A skin lesion imaged with a dermatoscope.
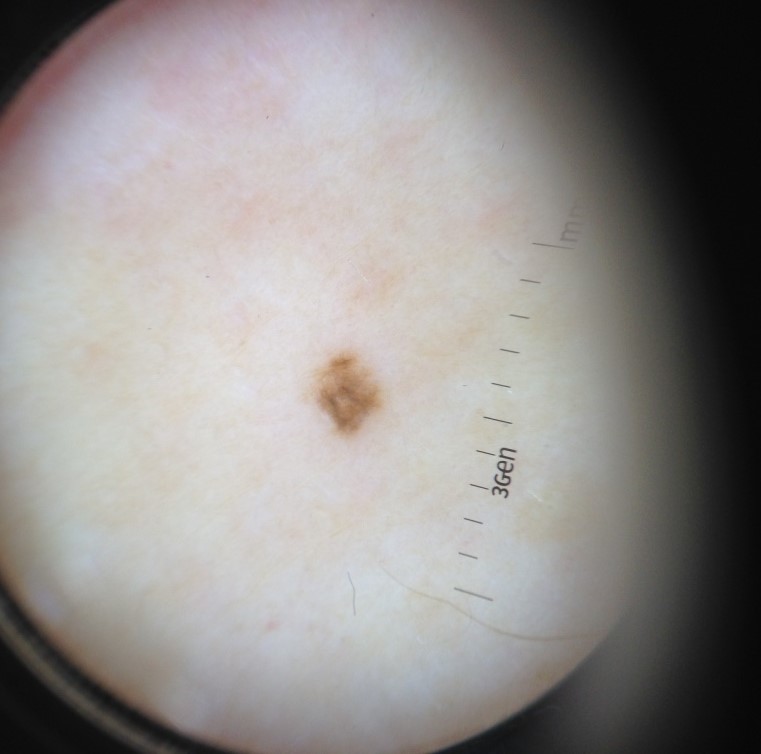The diagnostic label was a dysplastic junctional nevus.